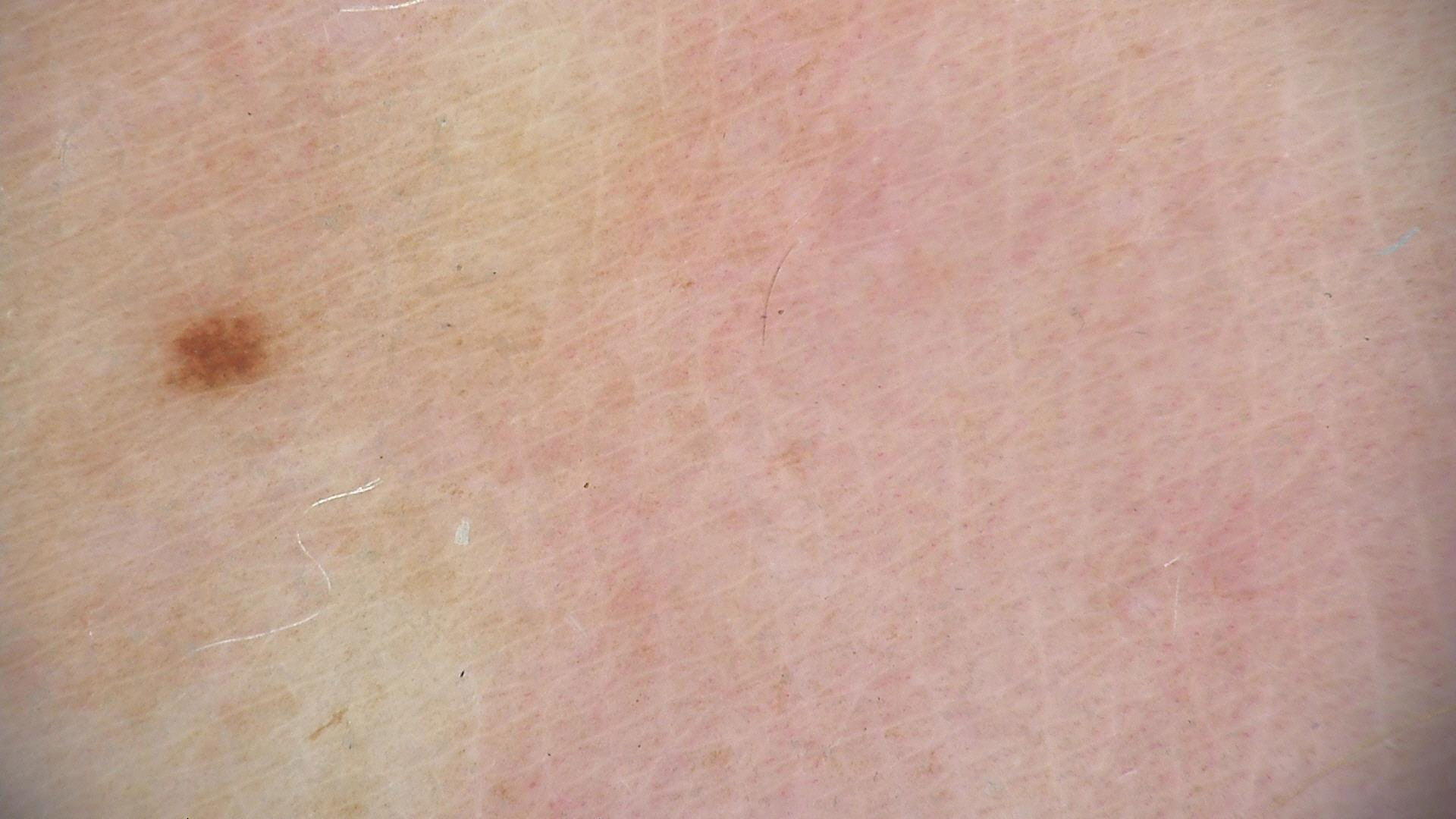A dermoscopic close-up of a skin lesion.
The diagnosis was a dysplastic junctional nevus.